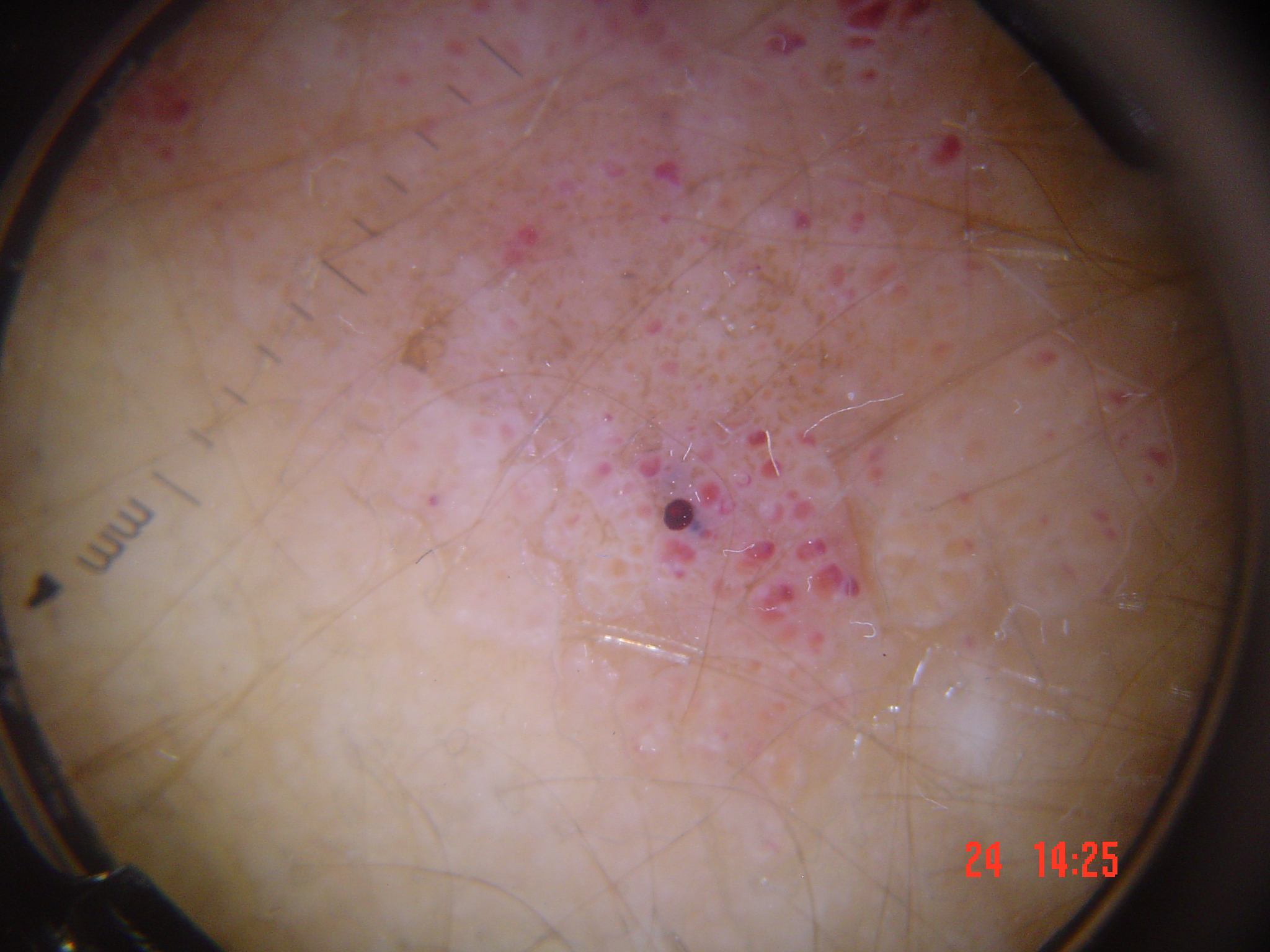image type: dermatoscopy; class: lymphangioma (expert consensus).